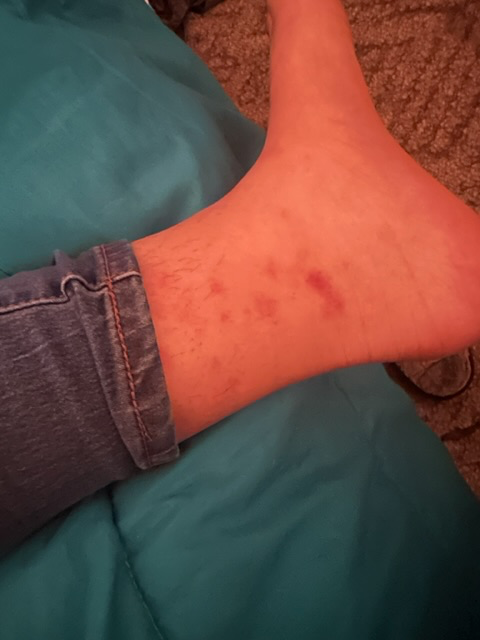The skin findings could not be characterized from the image.
The leg and top or side of the foot are involved.
The photograph is a close-up of the affected area.